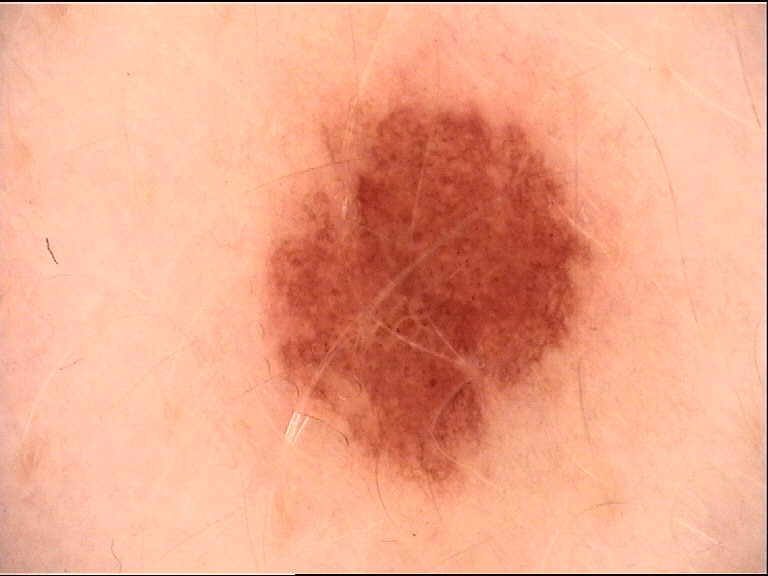imaging: dermatoscopy
category: banal
label: junctional nevus (expert consensus)